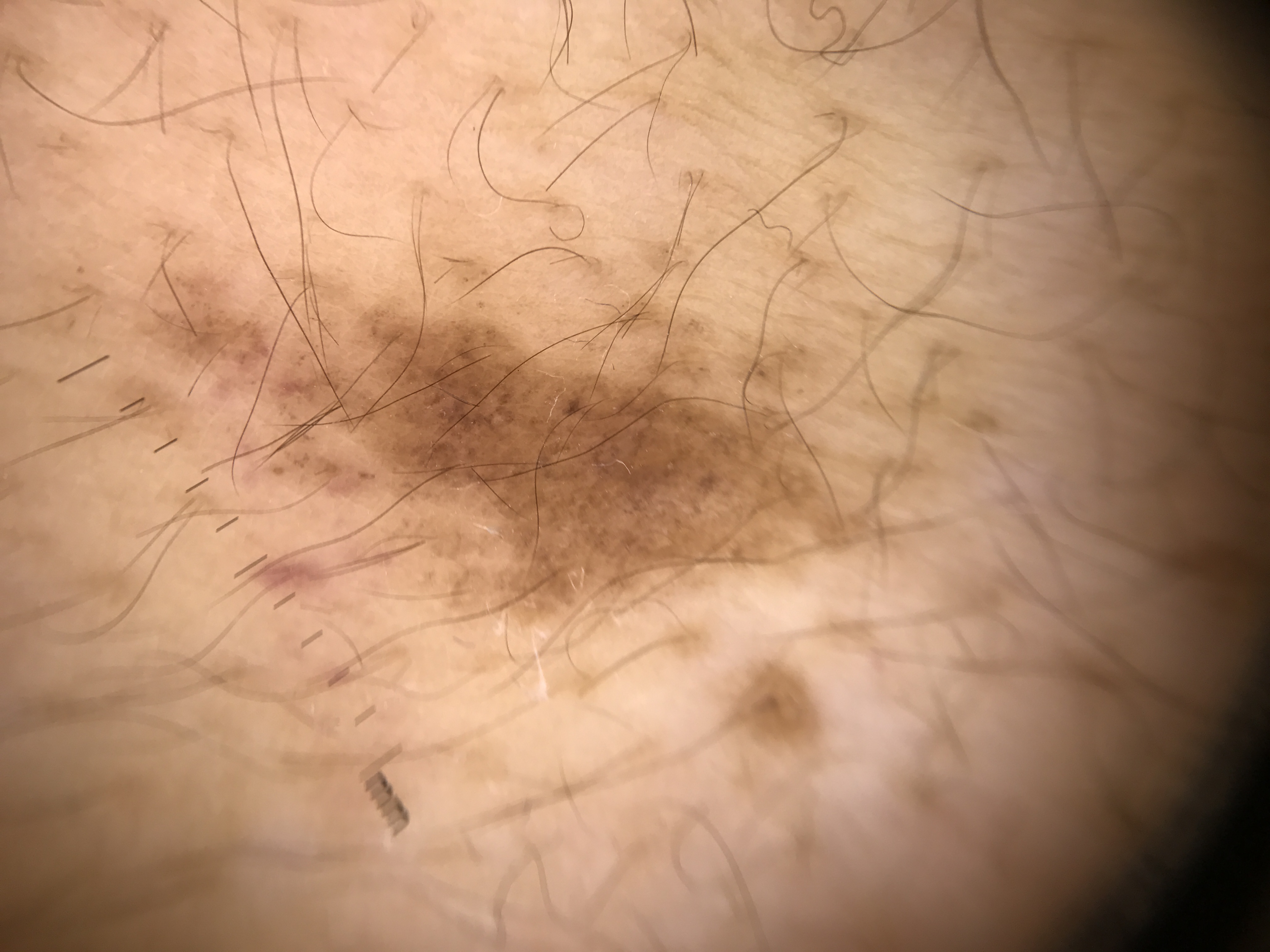image: dermatoscopy
diagnosis:
  name: dysplastic junctional nevus
  code: jd
  malignancy: benign
  super_class: melanocytic
  confirmation: expert consensus